A smartphone photograph of a skin lesion:
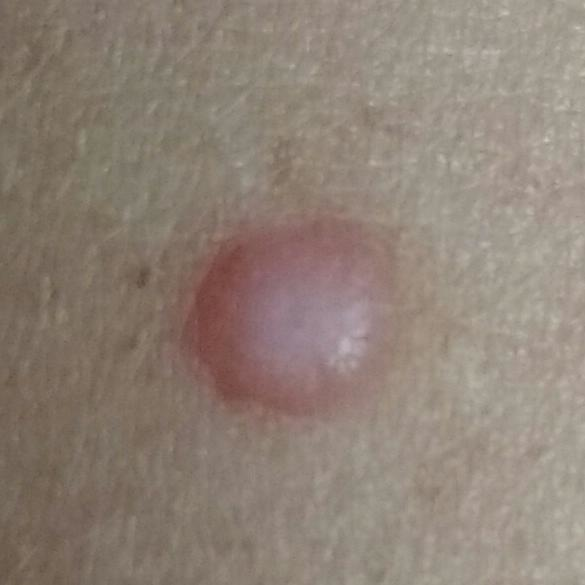The lesion is located on a forearm.
By the patient's account, the lesion is elevated, itches, and has grown, but has not bled and has not changed.
Clinically diagnosed as a nevus.